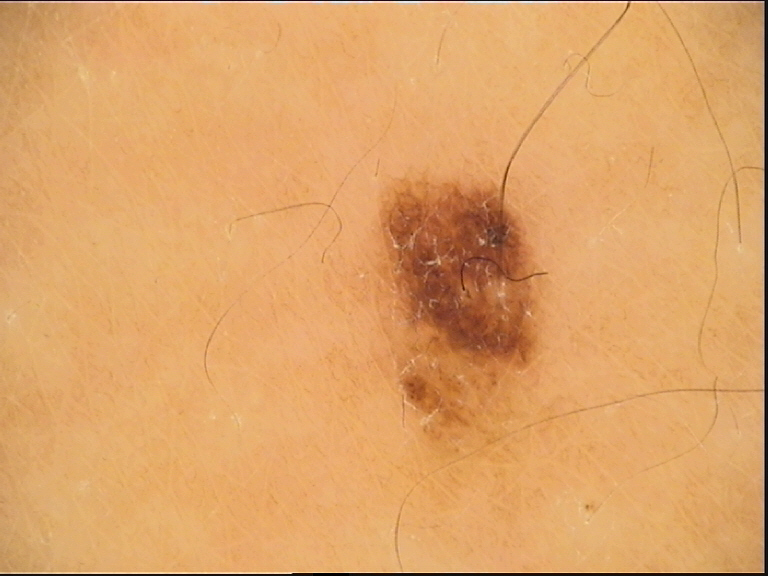The diagnostic label was a dysplastic junctional nevus.